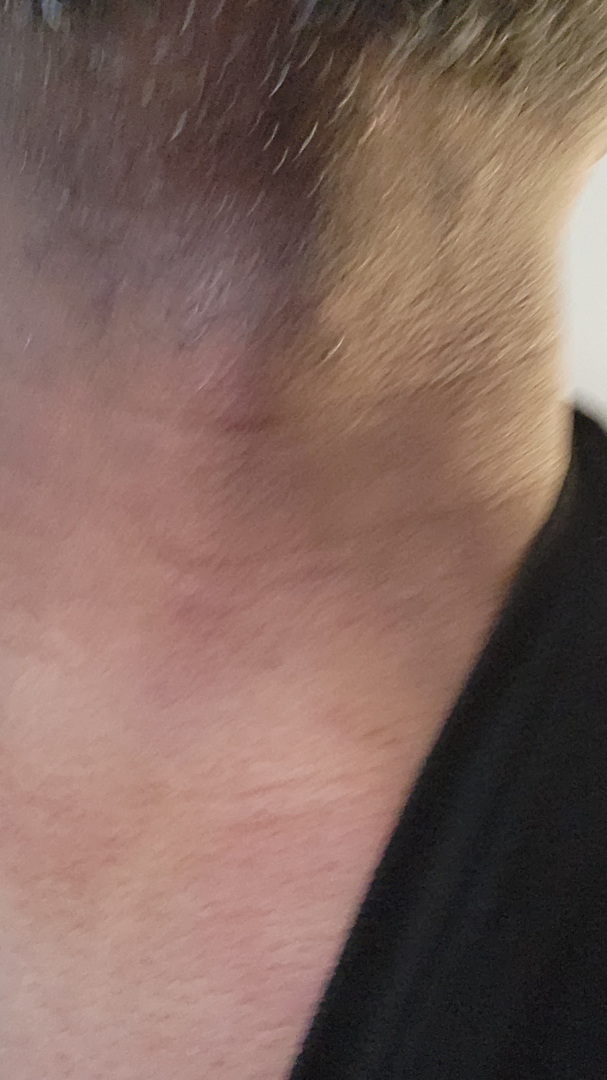Texture is reported as raised or bumpy. The photograph was taken at an angle.